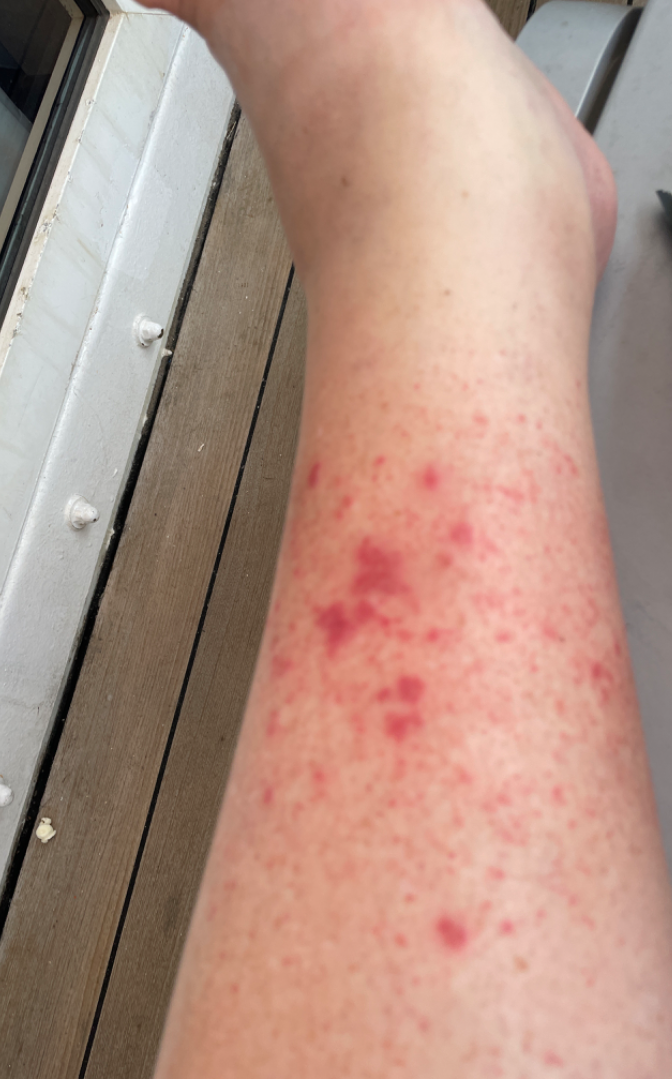Findings:
* impression: most consistent with Leukocytoclastic Vasculitis; also on the differential is Eczema